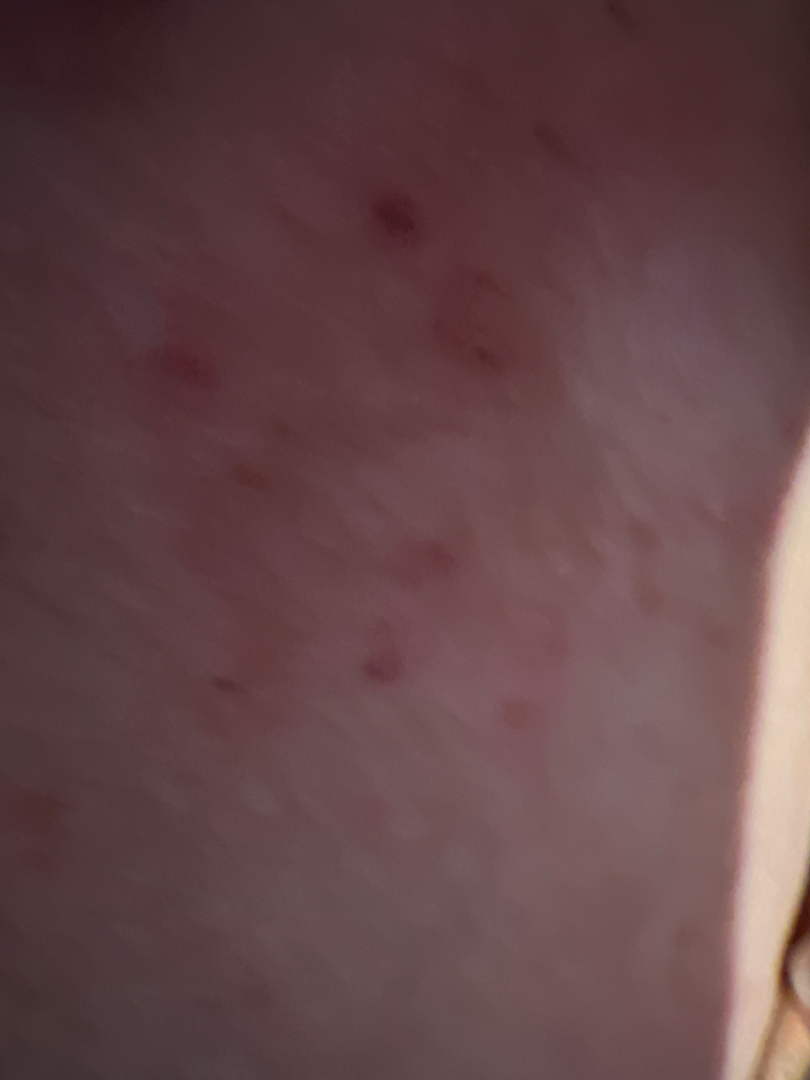Case summary:
– assessment · unable to determine
– subject · female, age 60–69
– skin tone · self-reported Fitzpatrick skin type IV
– shot type · close-up
– location · front of the torso, back of the torso and head or neck